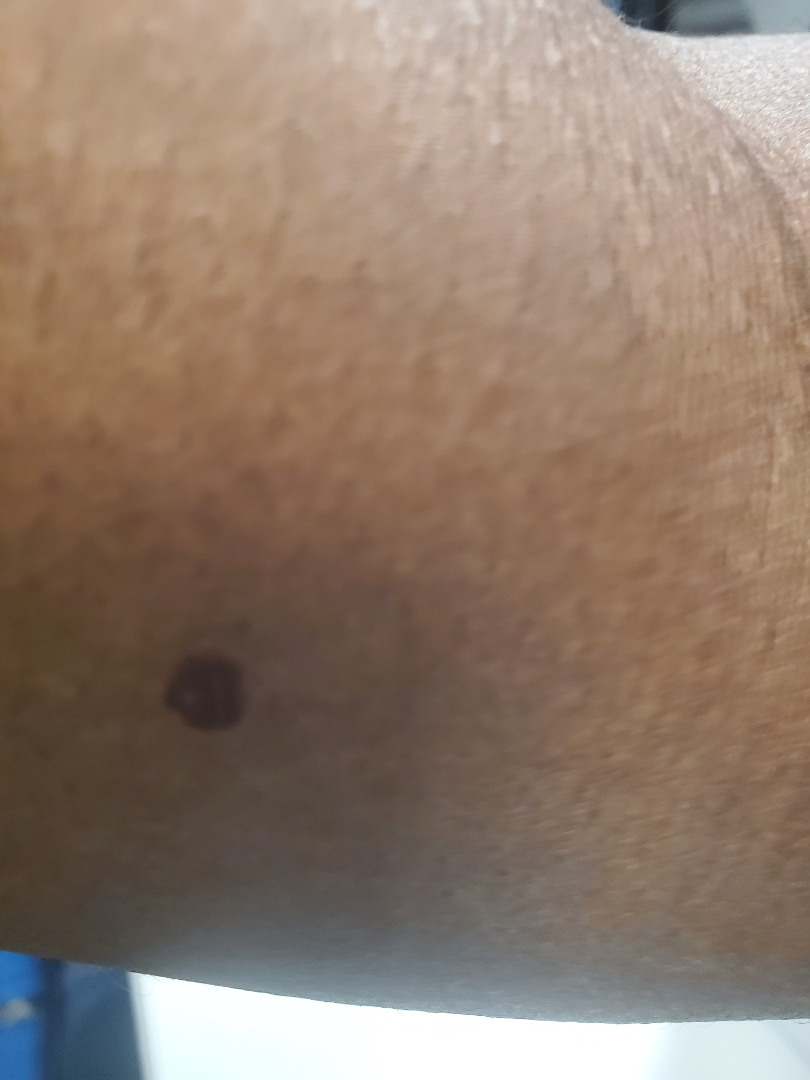The skin condition could not be confidently assessed from this image. The lesion is associated with darkening. Fitzpatrick phototype V; human graders estimated Monk Skin Tone 4 or 7 (two reviewer pools disagreed). A close-up photograph. The lesion involves the arm. The contributor notes the condition has been present for less than one week. No constitutional symptoms were reported.